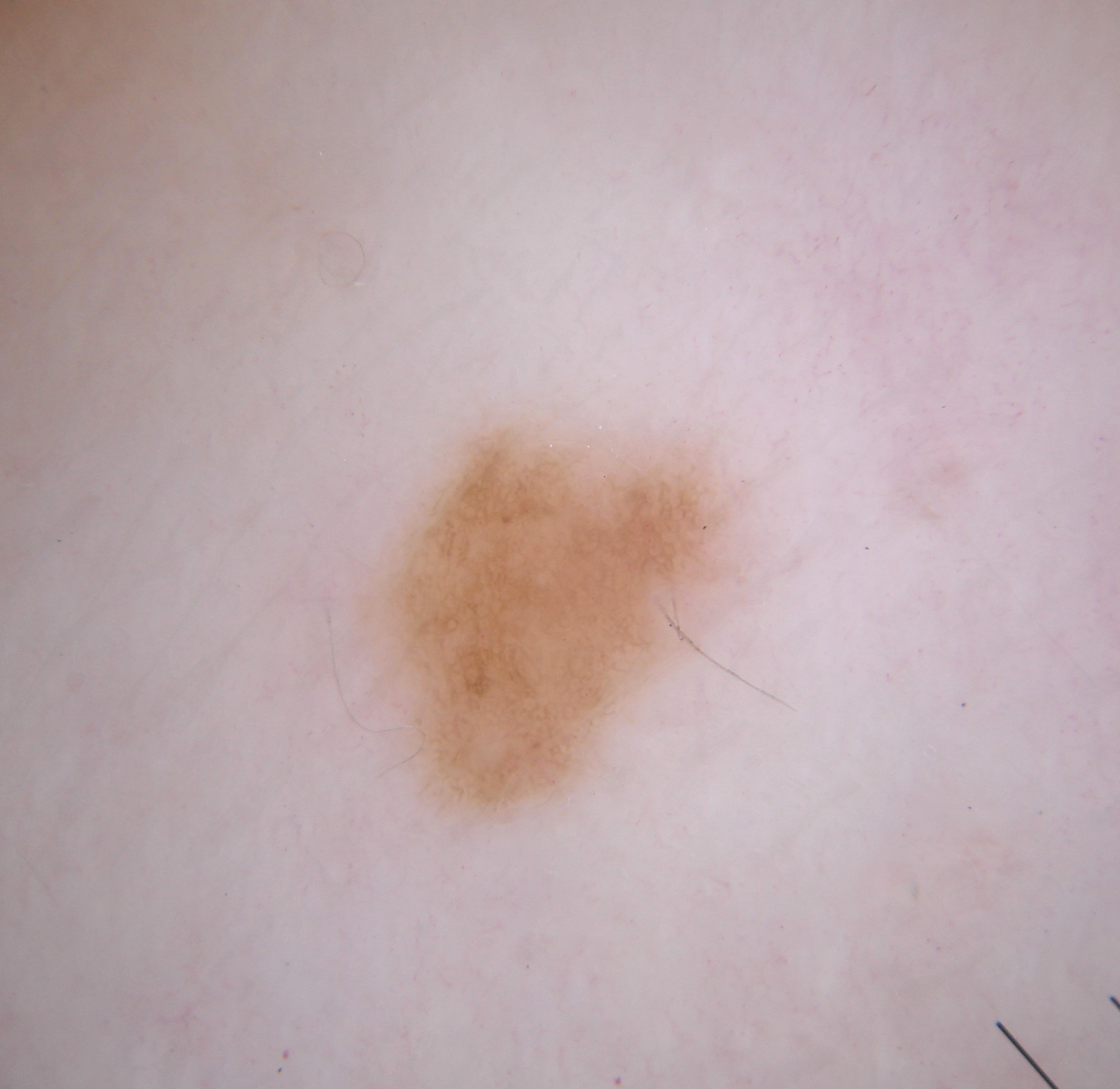Case summary:
- image type: dermoscopy
- bounding box: bbox(357, 432, 724, 822)
- features: pigment network
- lesion size: small
- impression: a melanocytic nevus, a benign skin lesion